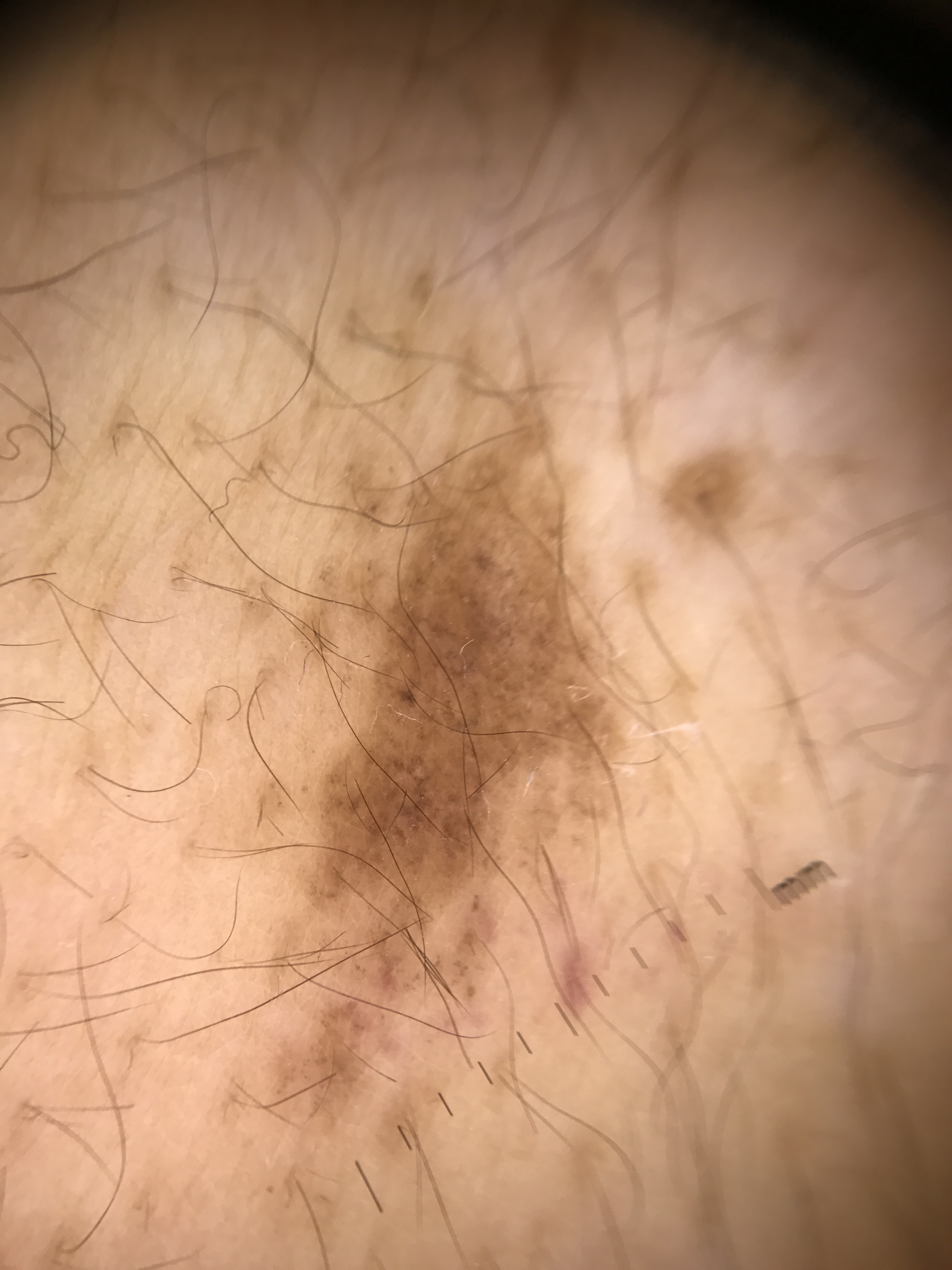A dermoscopic image of a skin lesion. Labeled as a banal lesion — a congenital junctional nevus.